A dermoscopic photograph of a skin lesion: 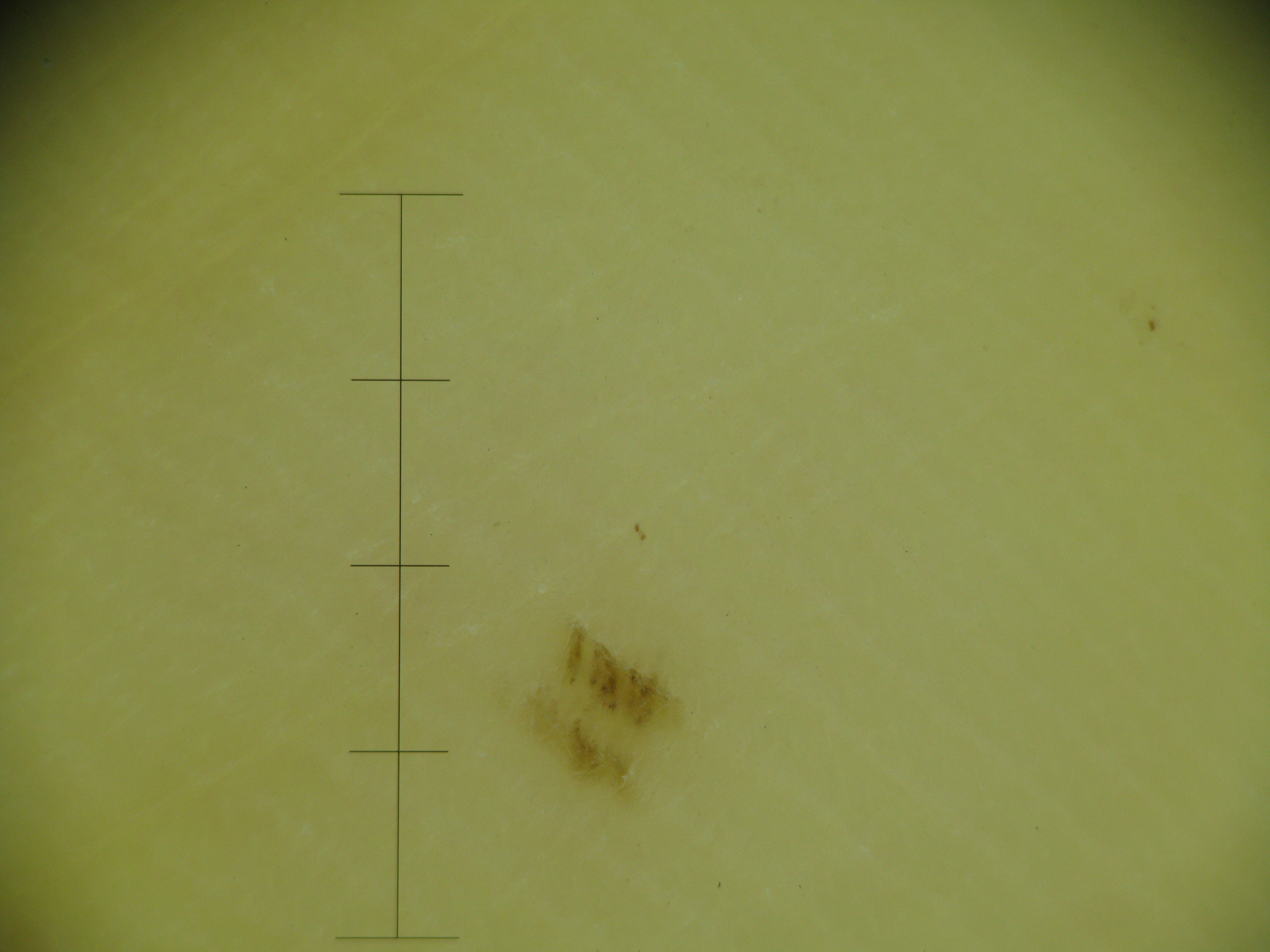Impression:
The diagnosis was a banal lesion — an acral junctional nevus.